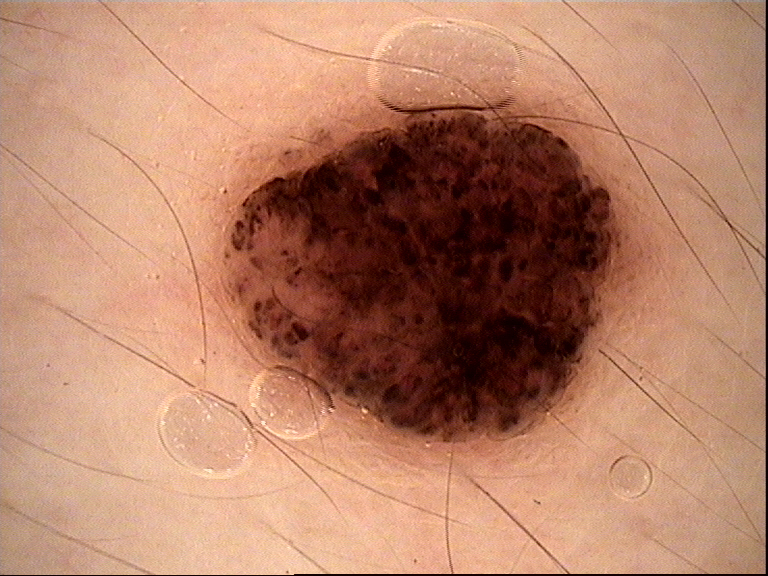A skin lesion imaged with a dermatoscope.
The morphology is that of a banal lesion.
Diagnosed as a compound nevus.